A dermatoscopic image of a skin lesion:
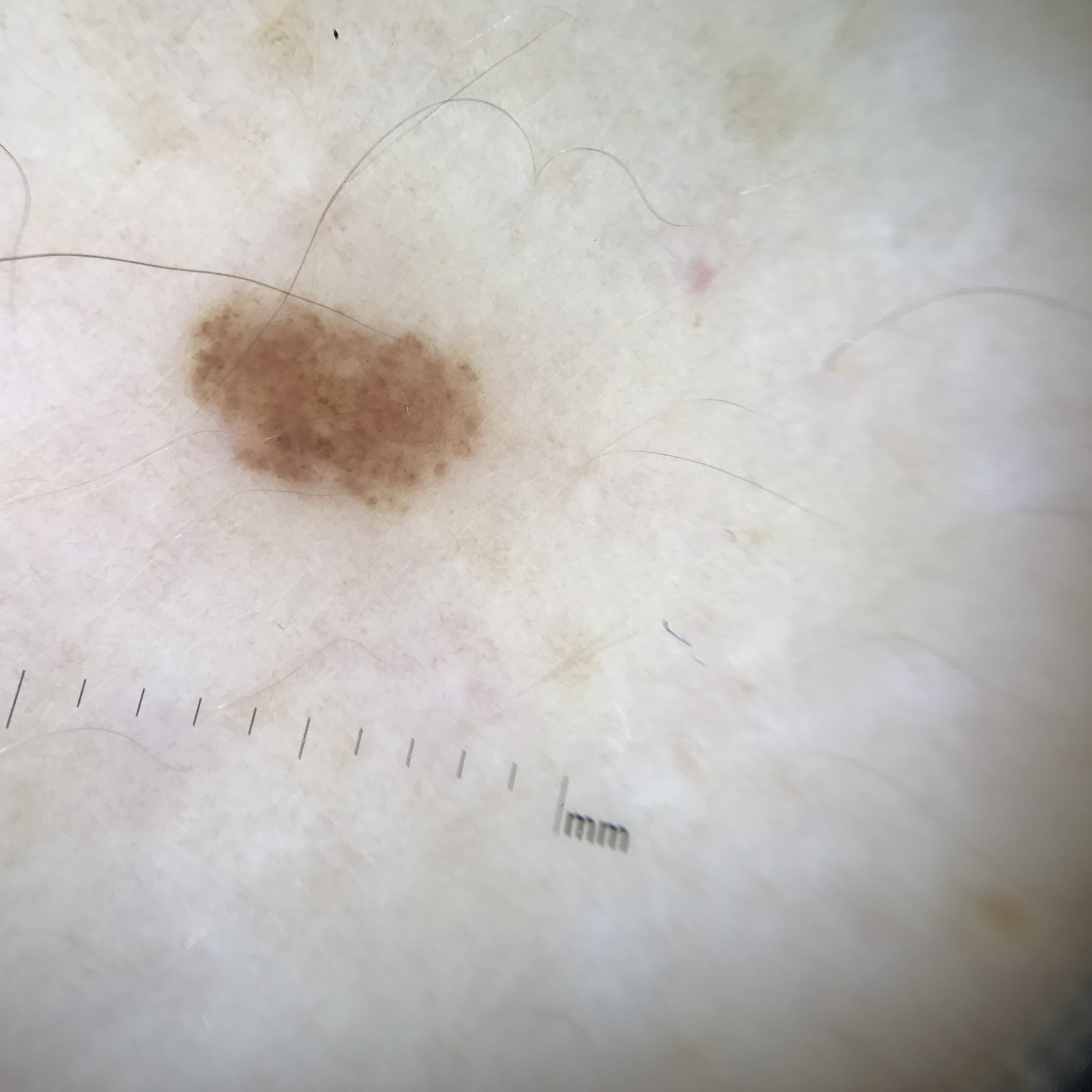Impression:
Classified as a dysplastic junctional nevus.